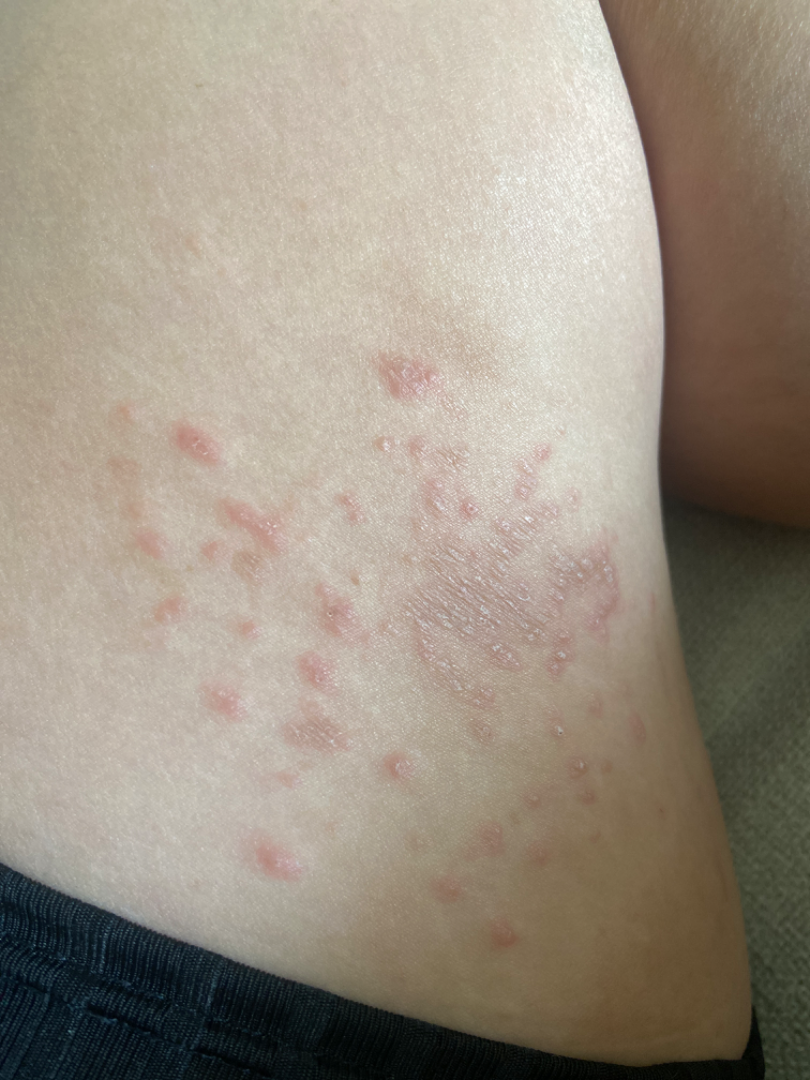Notes:
• photo taken · close-up
• subject · female, age 18–29
• symptom duration · one to four weeks
• other reported symptoms · none reported
• anatomic site · leg
• patient's own categorization · a rash
• lesion symptoms · darkening, enlargement, burning and itching
• differential · Psoriasis, Lichen planus/lichenoid eruption and Eczema were considered with similar weight; less probable is Insect Bite; a more distant consideration is Allergic Contact Dermatitis